A dermoscopic photograph of a skin lesion: 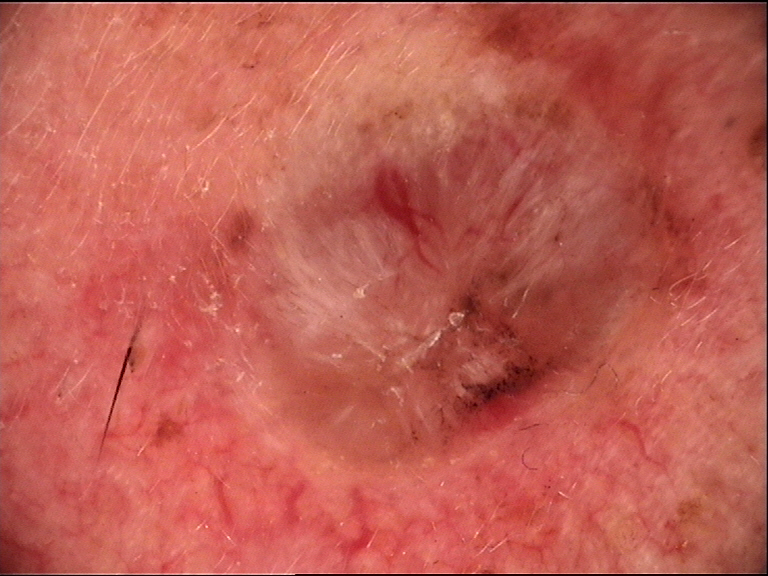Findings:
* class · basal cell carcinoma (biopsy-proven)